A dermoscopic close-up of a skin lesion. The chart documents a previous melanoma but no melanoma in first-degree relatives — 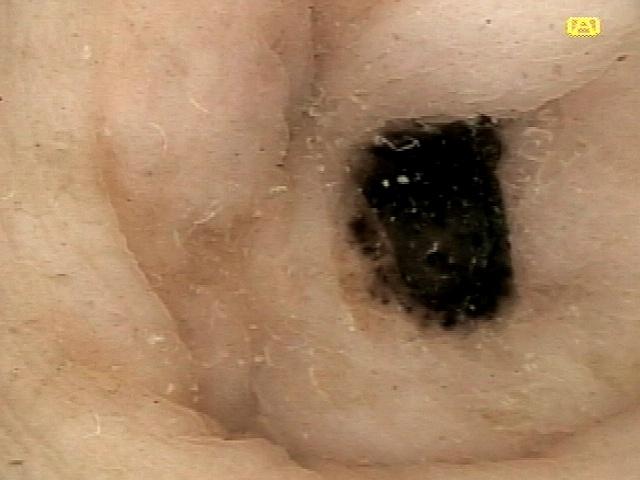Findings: The lesion involves the trunk. Pathology: On biopsy, the diagnosis was a lesion of melanocytic origin — a nevus.